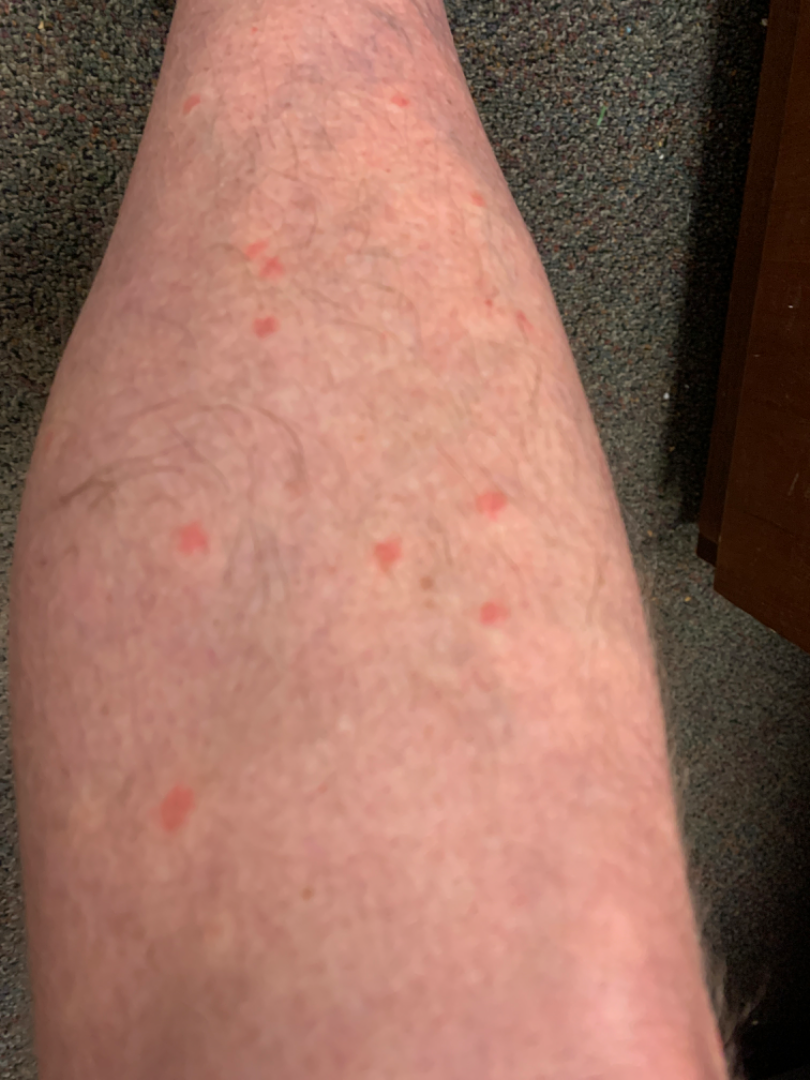This is a close-up image.
On photographic review, Insect Bite (most likely); Urticaria (considered); Eczema (unlikely).